Close-up view. The lesion is described as raised or bumpy. The contributor notes the condition has been present for less than one week. The patient considered this skin that appeared healthy to them. The leg is involved. No relevant systemic symptoms — 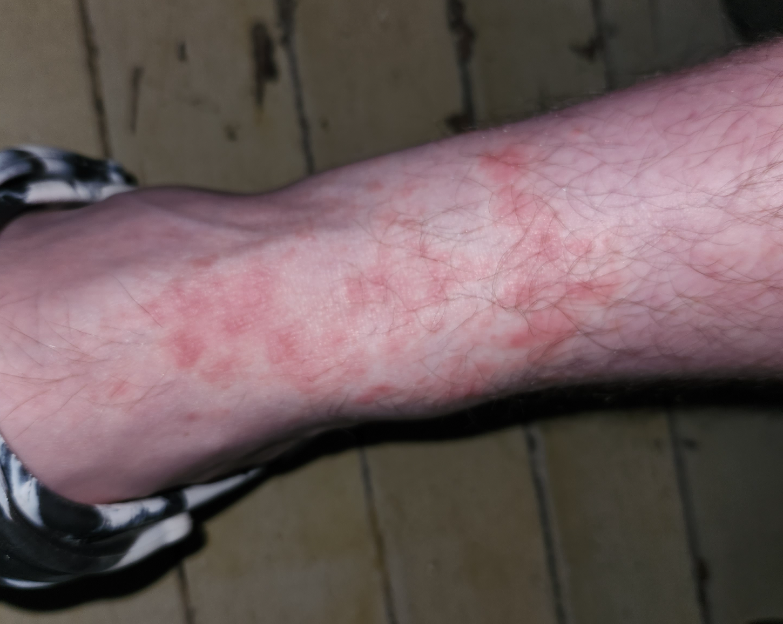dermatologist impression = Eczema (possible); Allergic Contact Dermatitis (possible)